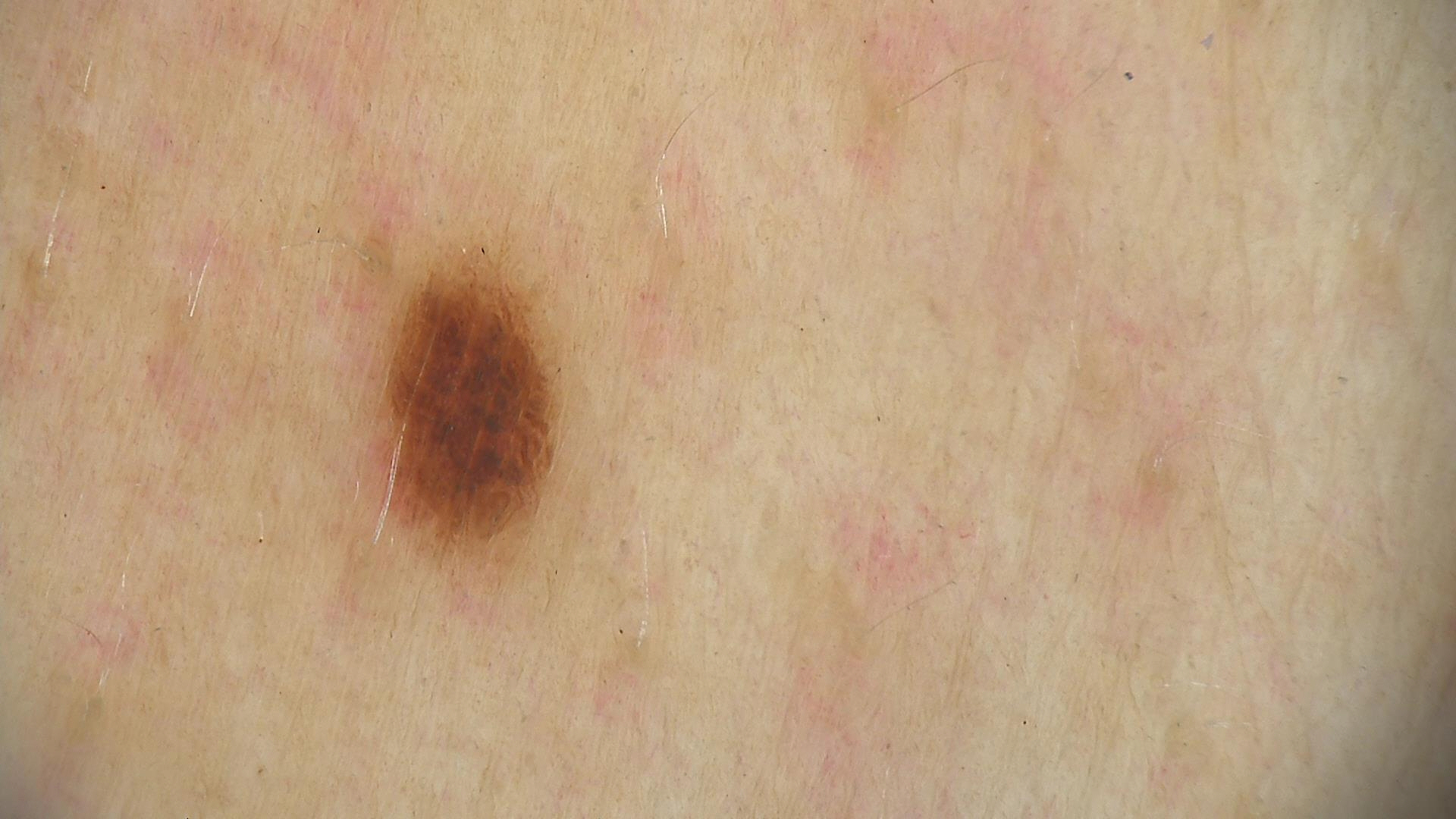Classified as a dysplastic junctional nevus.